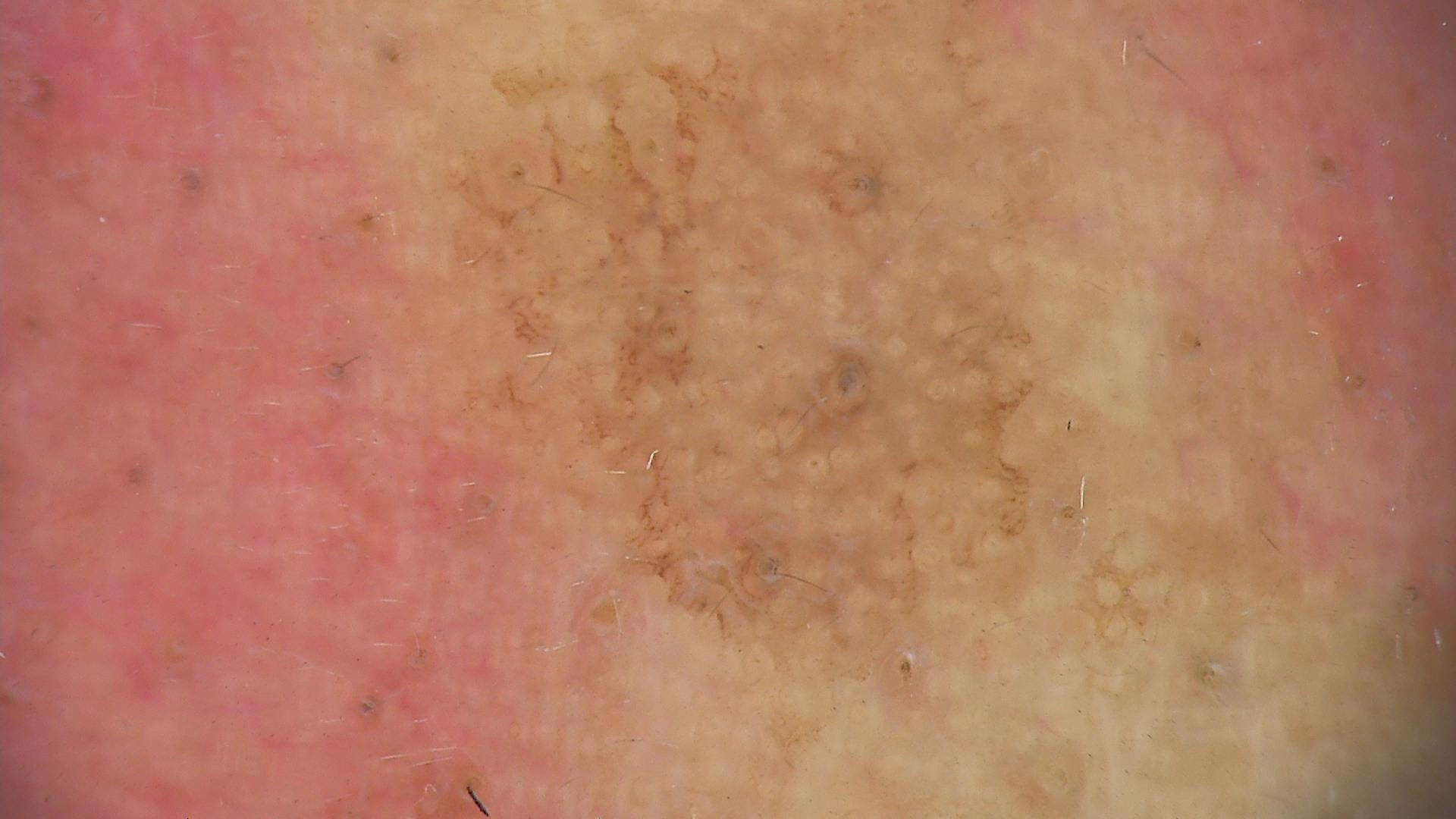Case:
Dermoscopy of a skin lesion.
Conclusion:
The diagnosis was a premalignant, keratinocytic lesion — an actinic keratosis.